Dermoscopy of a skin lesion: 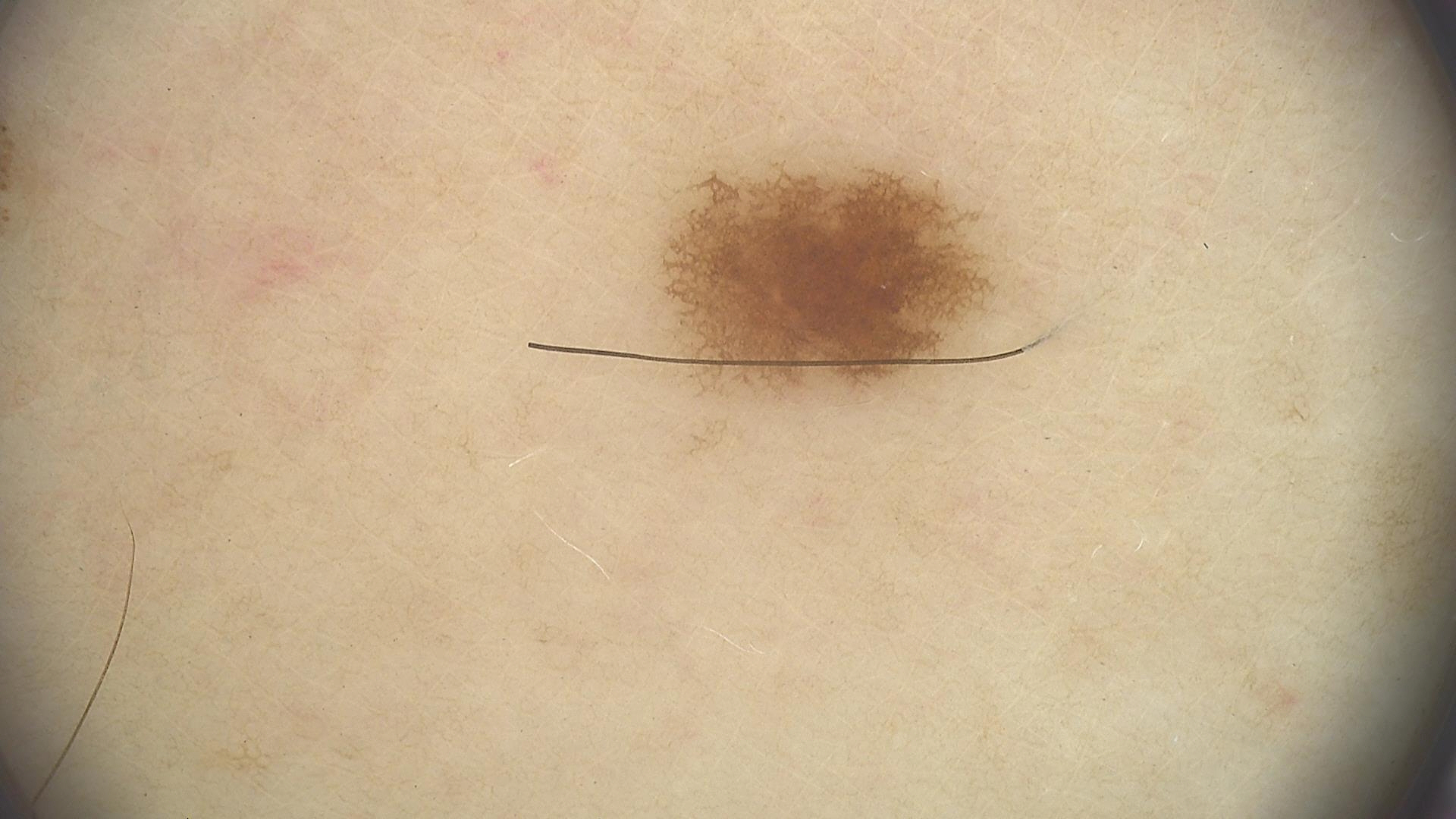label = junctional nevus (expert consensus).